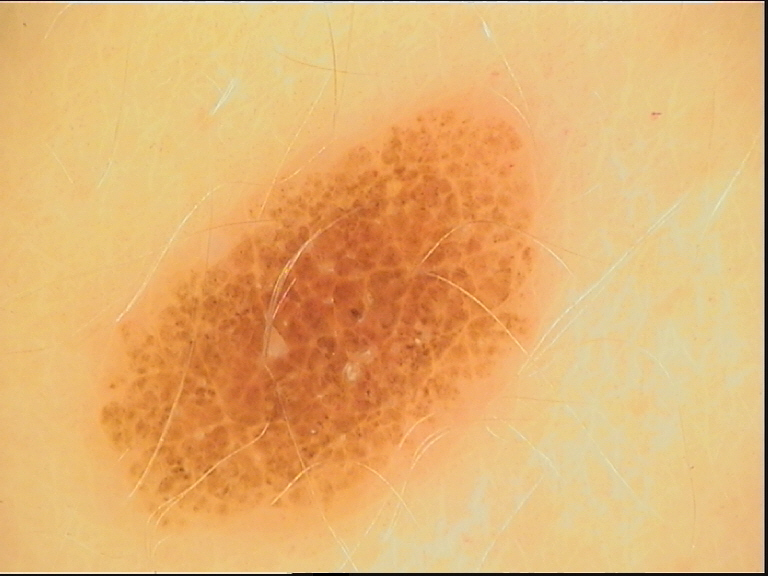<dermoscopy>
  <image>dermoscopy</image>
  <diagnosis>
    <name>dysplastic compound nevus</name>
    <code>cd</code>
    <malignancy>benign</malignancy>
    <super_class>melanocytic</super_class>
    <confirmation>expert consensus</confirmation>
  </diagnosis>
</dermoscopy>